A female patient aged approximately 25; a dermoscopy image of a single skin lesion — 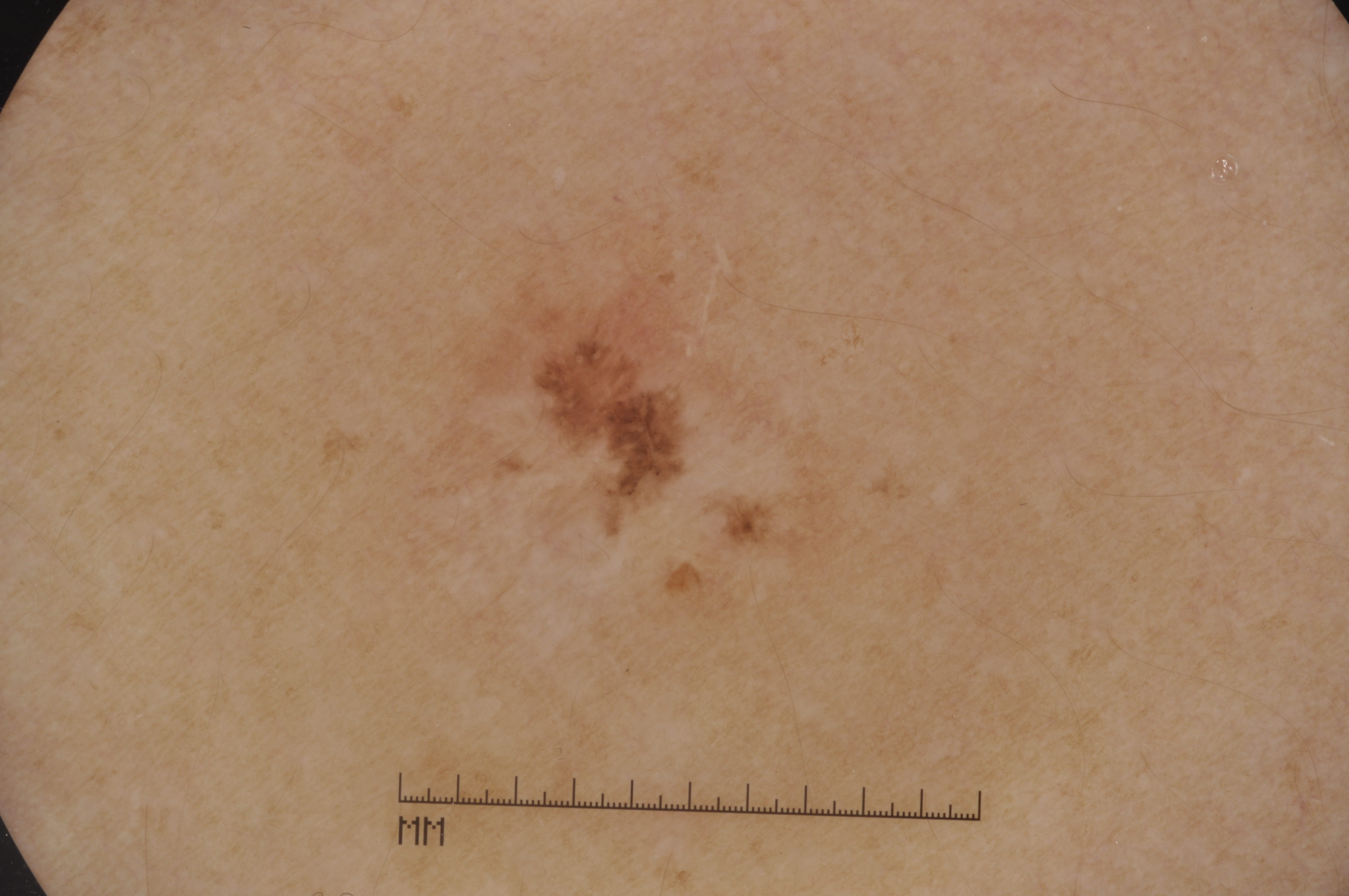A mid-sized lesion within the field. Dermoscopically, the lesion shows no streaks, negative network, milia-like cysts, or pigment network. As (left, top, right, bottom), the lesion's extent is bbox=[405, 147, 855, 684]. Consistent with a melanocytic nevus, a benign skin lesion.